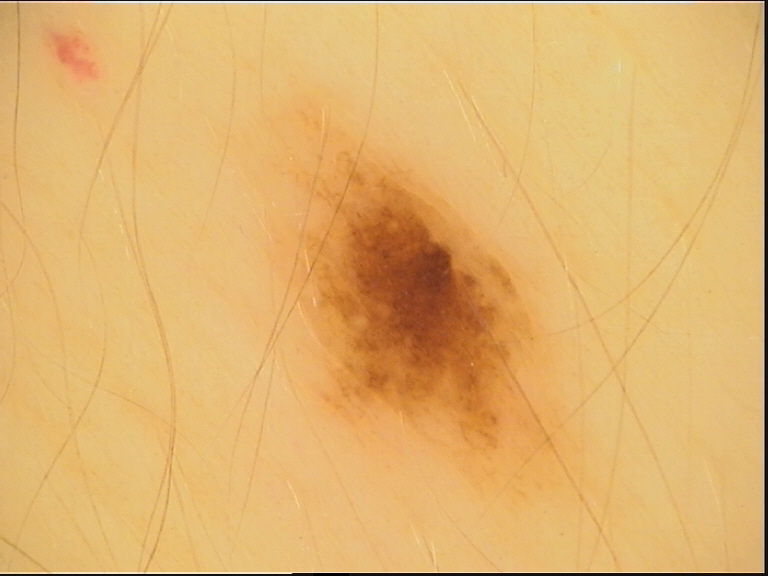Summary:
A dermoscopic photograph of a skin lesion.
Conclusion:
Consistent with a benign lesion — a dysplastic junctional nevus.